A skin lesion imaged with a dermatoscope.
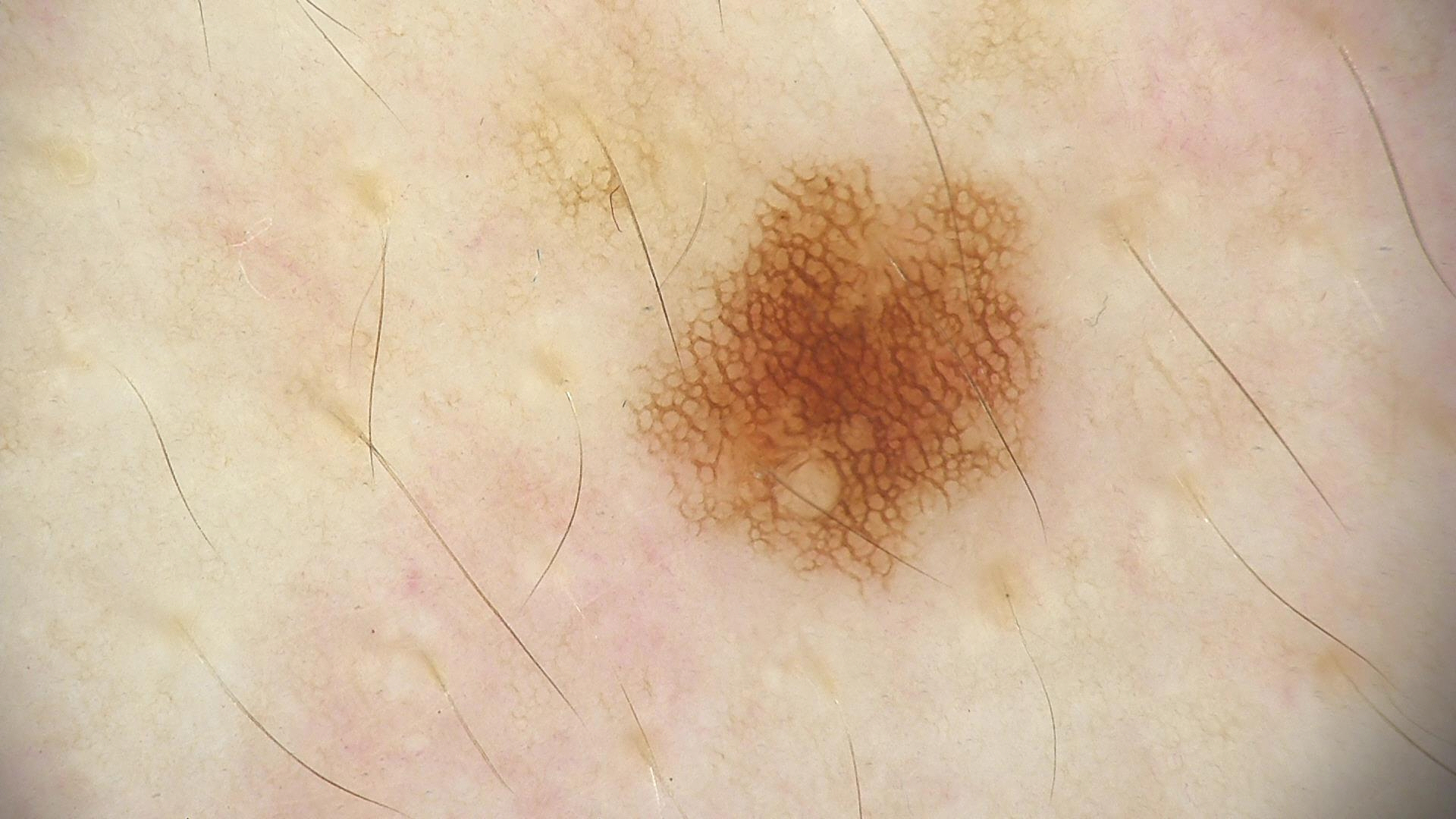Impression:
The diagnosis was a dysplastic junctional nevus.